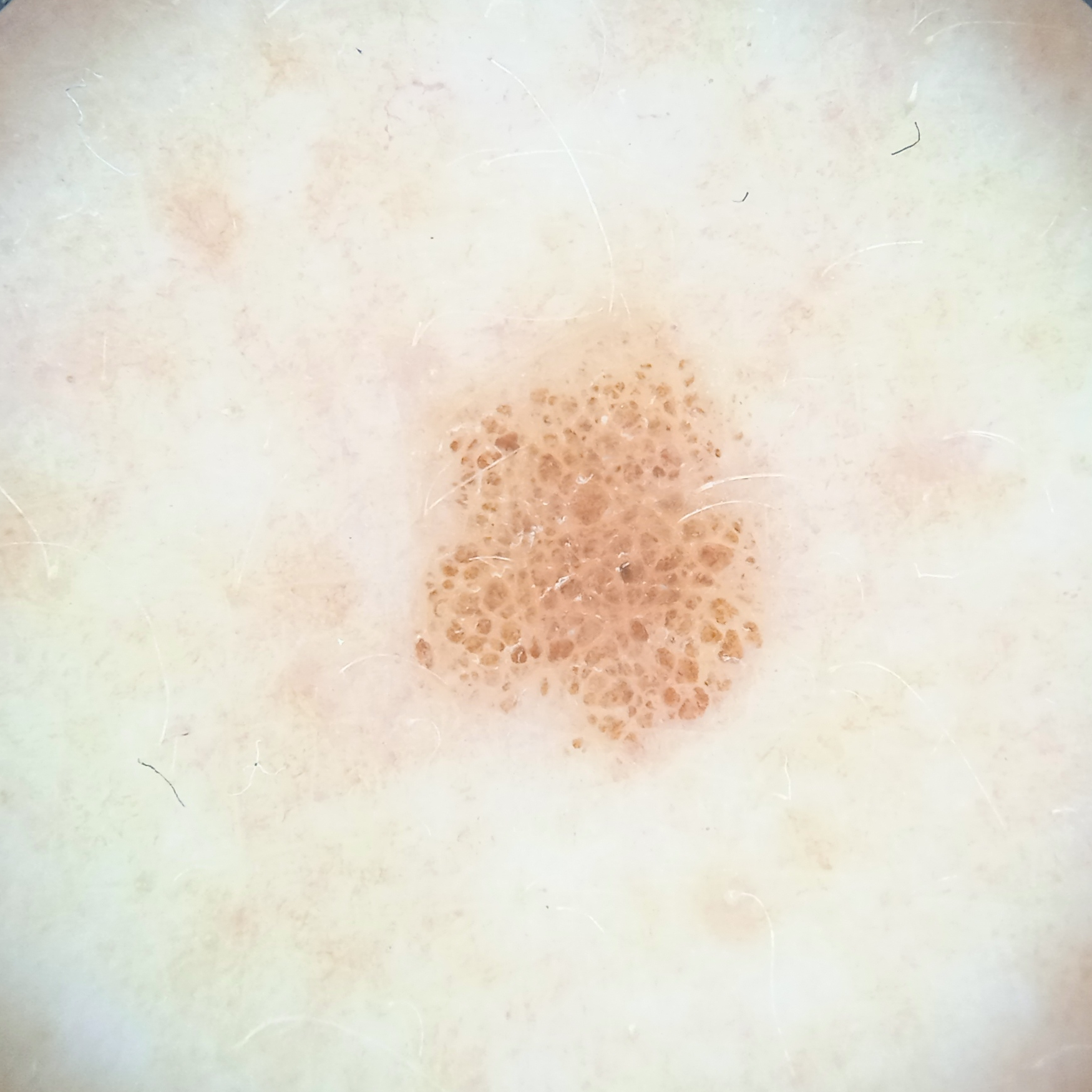The patient reports a personal history of skin cancer. A female subject 50 years old. The patient says their skin reddens with sun exposure. A moderate number of moles by the patient's own estimate. Acquired for a research image collection, with no referral diagnosis. The lesion is on the back. The lesion is about 5.1 mm across. The dermatologists' assessment was a melanocytic nevus.